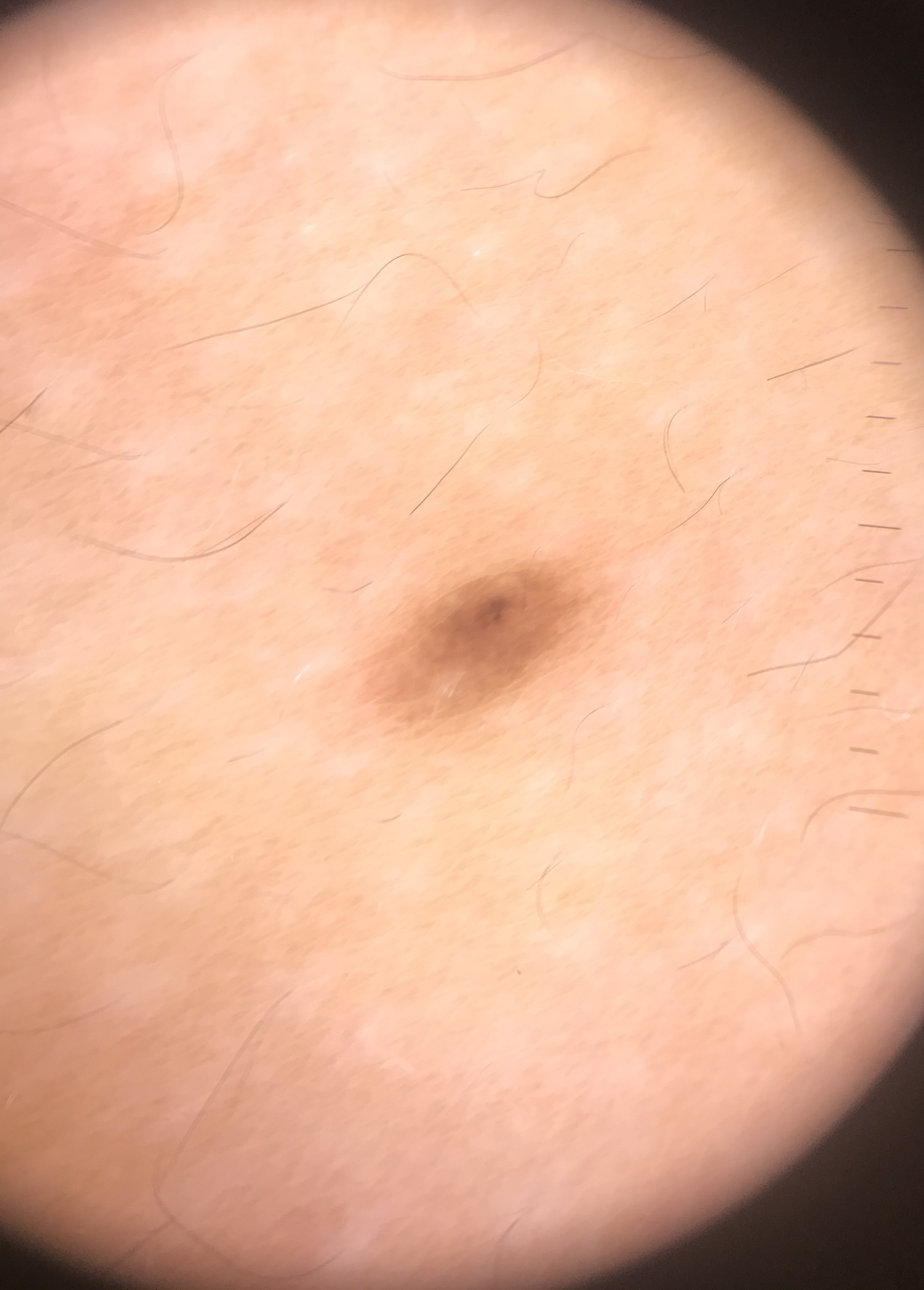assessment: junctional nevus (expert consensus).